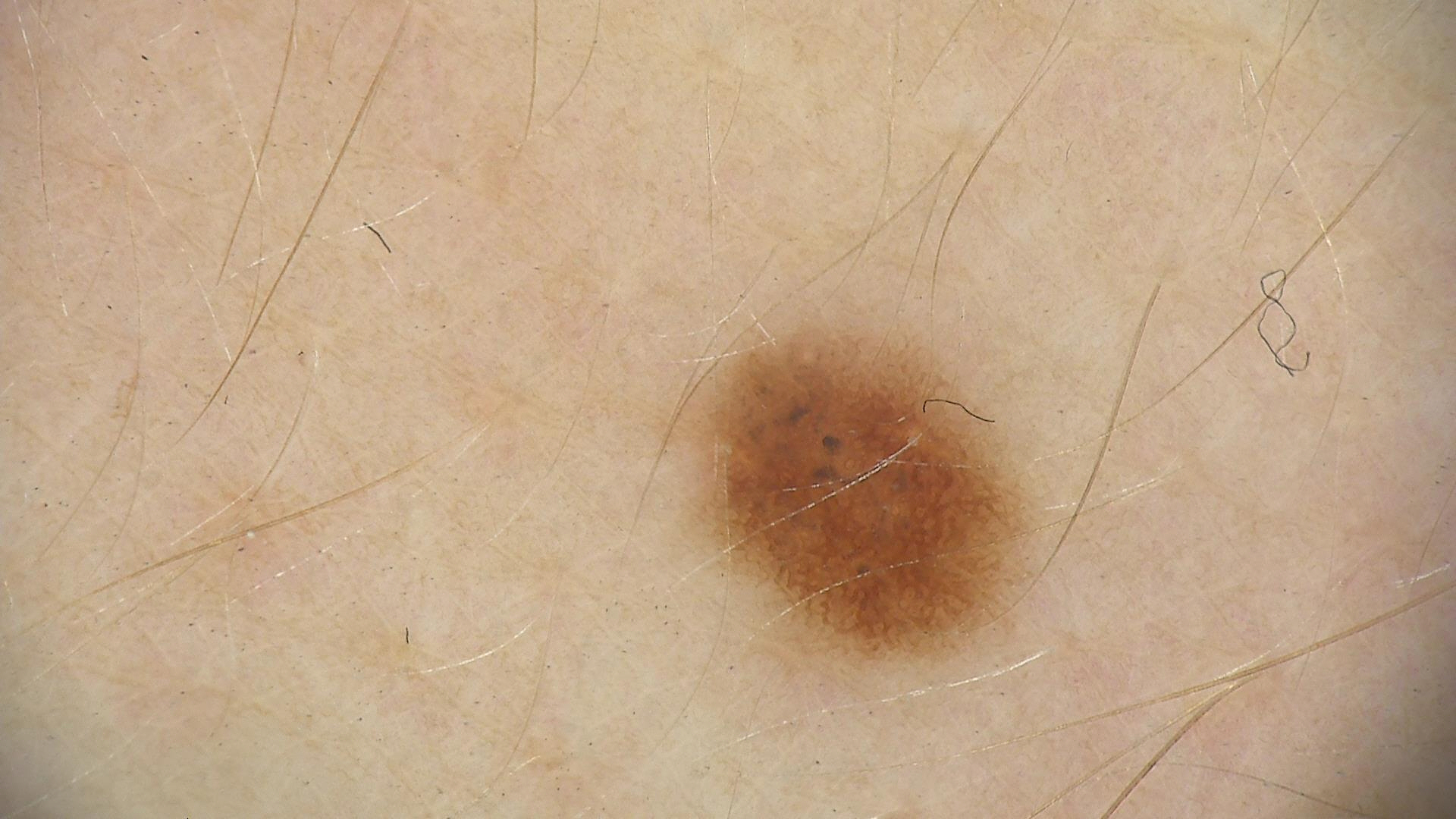{
  "diagnosis": {
    "name": "dysplastic junctional nevus",
    "code": "jd",
    "malignancy": "benign",
    "super_class": "melanocytic",
    "confirmation": "expert consensus"
  }
}